The affected area is the head or neck, this image was taken at an angle:
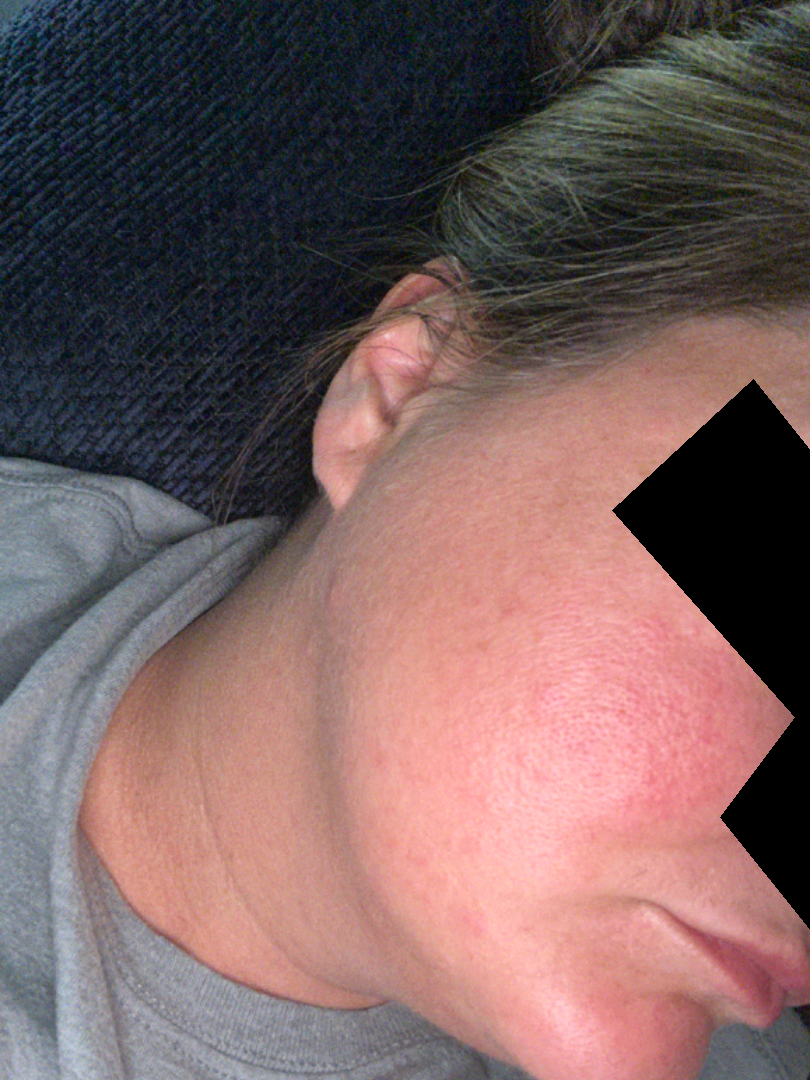differential diagnosis = one reviewing dermatologist: Rosacea and Flushing were each considered, in no particular order; a remote consideration is Cutaneous lupus.